Recorded as FST III. A female subject in their late 50s. The chart notes prior skin cancer (patient or family), prior malignancy (patient or family), and no tobacco use. A smartphone photograph of a skin lesion:
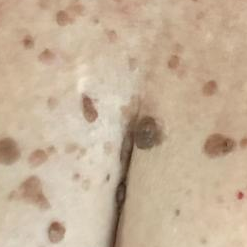Q: Where on the body is the lesion?
A: the chest
Q: How large is the lesion?
A: approx. 17 × 15 mm
Q: What does the patient describe?
A: growth, elevation
Q: What is this lesion?
A: seborrheic keratosis (clinical consensus)